A dermoscopic close-up of a skin lesion.
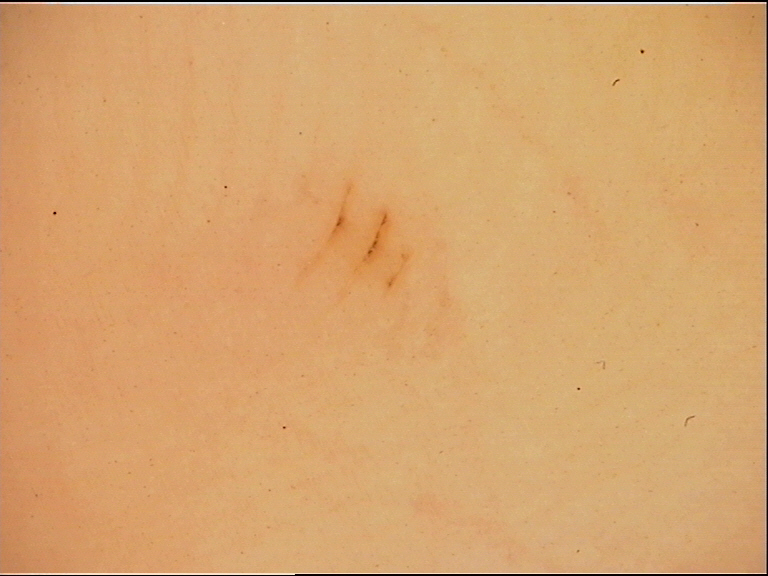Diagnosed as an acral junctional nevus.